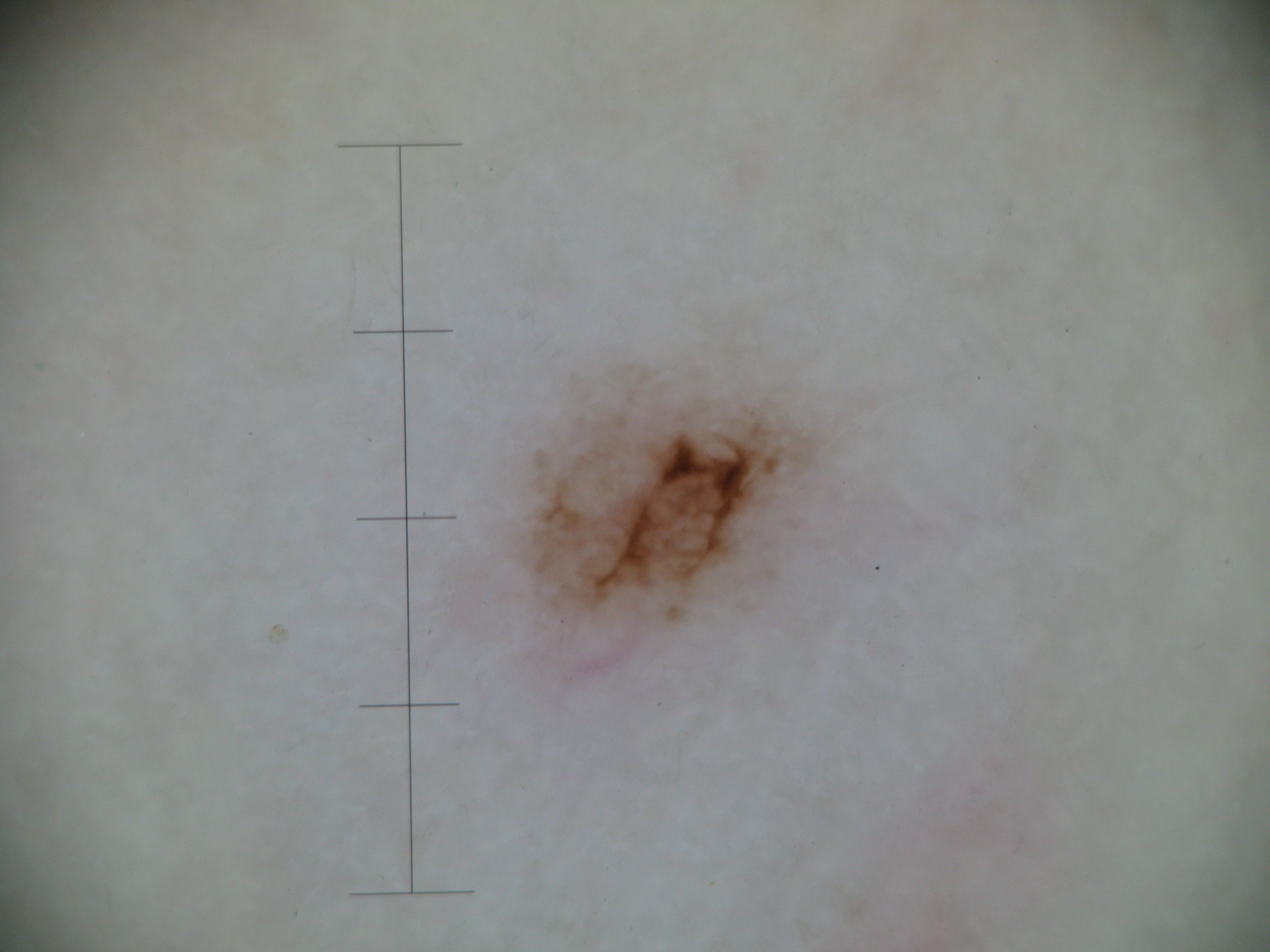Classified as an acral dysplastic junctional nevus.